A clinical photo of a skin lesion taken with a smartphone; a female patient 71 years old: 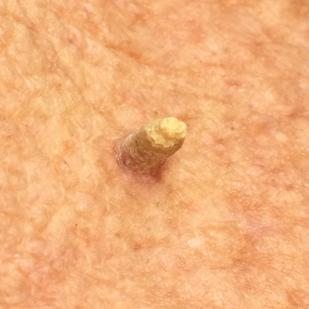Findings:
• symptoms: growth, elevation
• diagnosis: actinic keratosis (biopsy-proven)